The patient reported no systemic symptoms · the photograph is a close-up of the affected area · female contributor, age 40–49 · the patient indicates the condition has been present for one to four weeks · the affected area is the front of the torso:
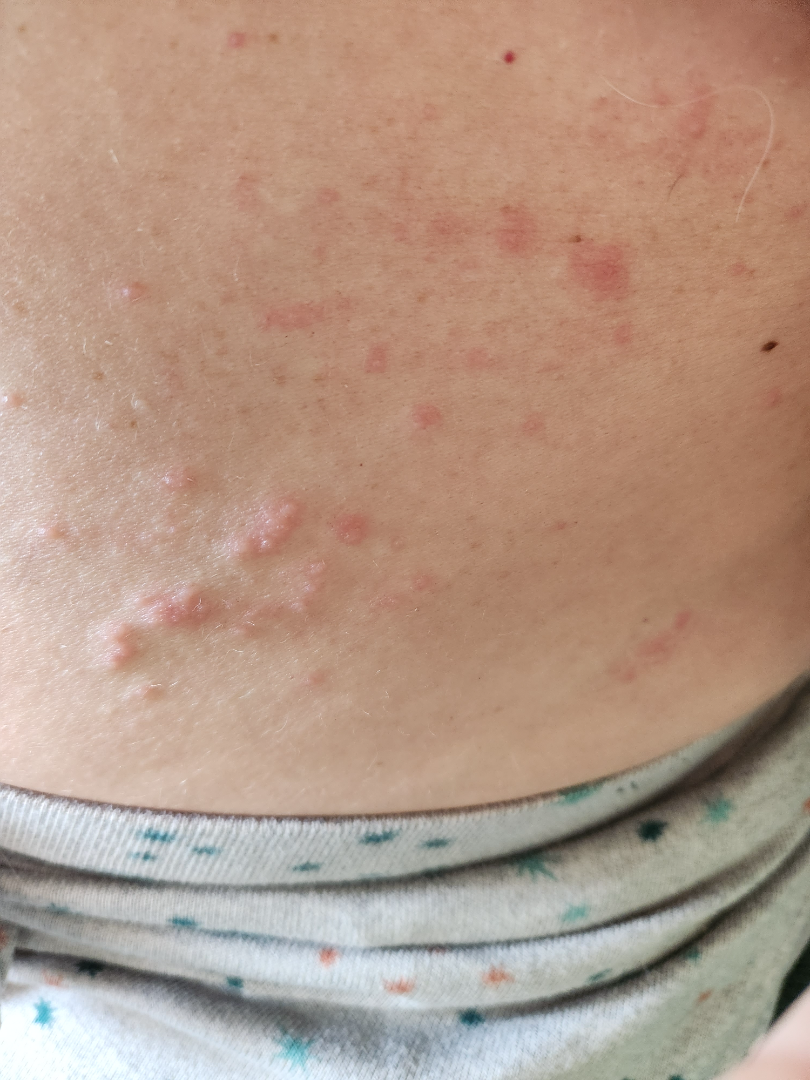| key | value |
|---|---|
| differential | the leading impression is Irritant Contact Dermatitis; also raised was Herpes Zoster; possibly Allergic Contact Dermatitis; a remote consideration is Eczema |